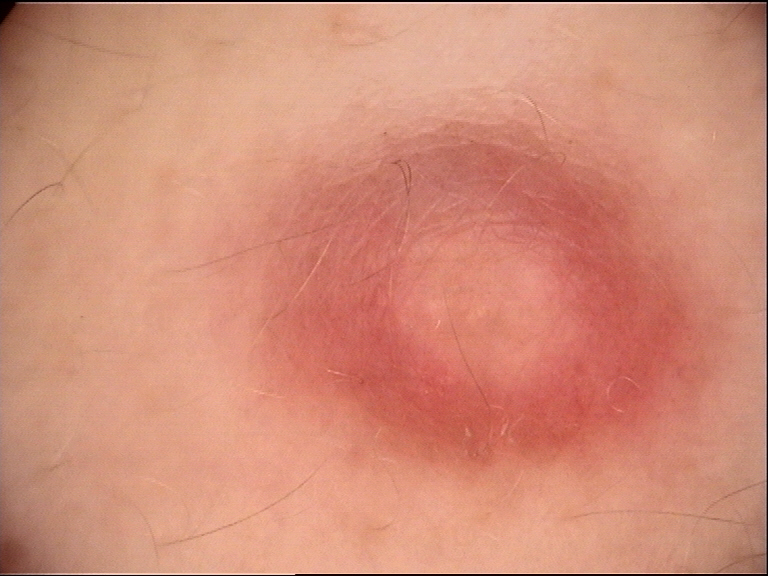Consistent with a benign, fibro-histiocytic lesion — a dermatofibroma.